The patient indicates darkening · the patient considered this a rash · the patient reported no systemic symptoms · the lesion involves the arm · an image taken at a distance · FST III; lay graders estimated MST 3 · the contributor is a female aged 18–29 · the patient indicates the lesion is raised or bumpy and flat · the condition has been present for one to four weeks — 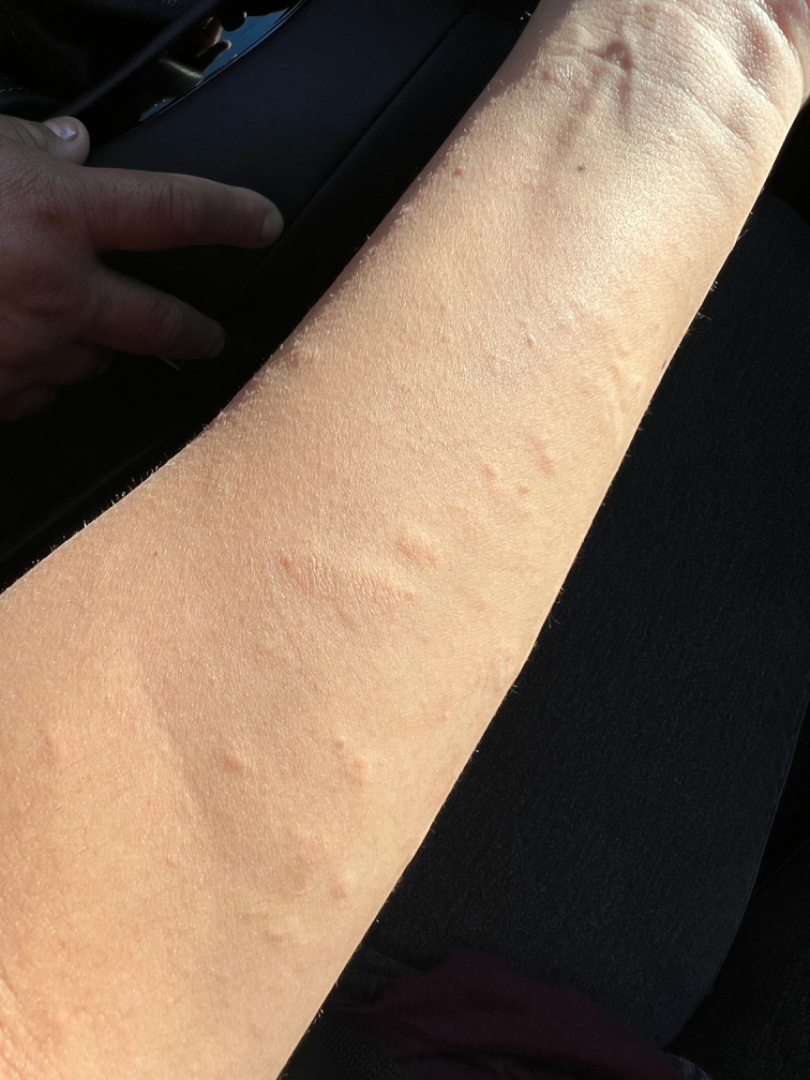One reviewing dermatologist: the favored diagnosis is Urticaria; also consider Acute and chronic dermatitis.